The photograph was taken at a distance: 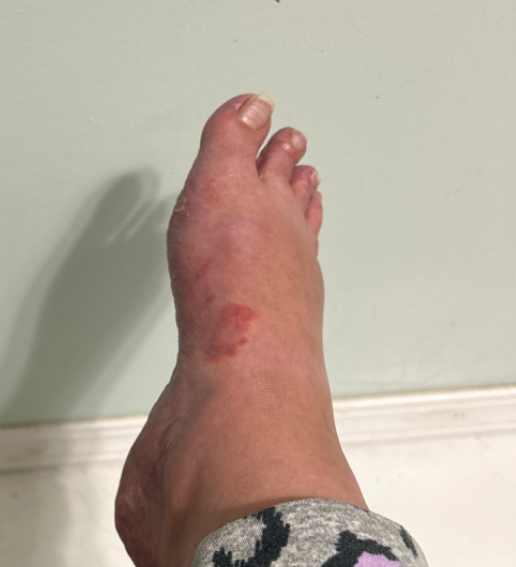Granuloma annulare (weight 1.00).